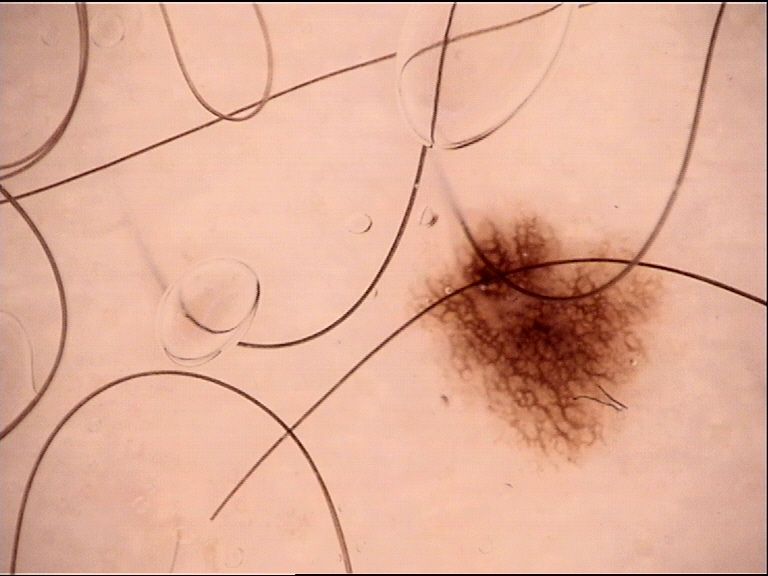label: dysplastic junctional nevus (expert consensus).